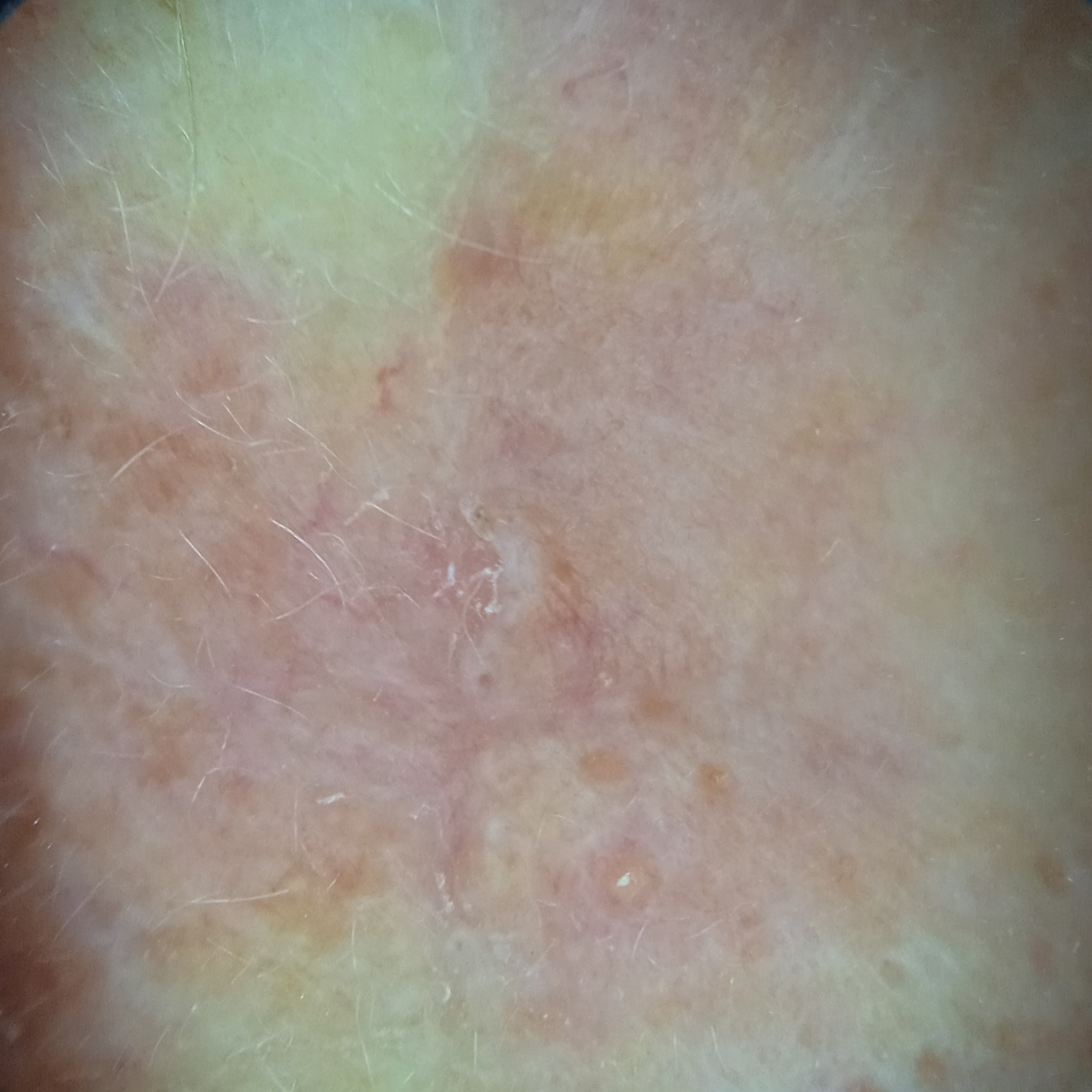Q: Patient demographics?
A: female, 68 years old
Q: What is the imaging modality?
A: dermatoscopic image
Q: What is the referral context?
A: research study (no referral diagnosis)
Q: Where is the lesion?
A: the face
Q: Lesion size?
A: 9.9 mm
Q: What was the diagnosis?
A: actinic keratosis (dermatologist consensus)